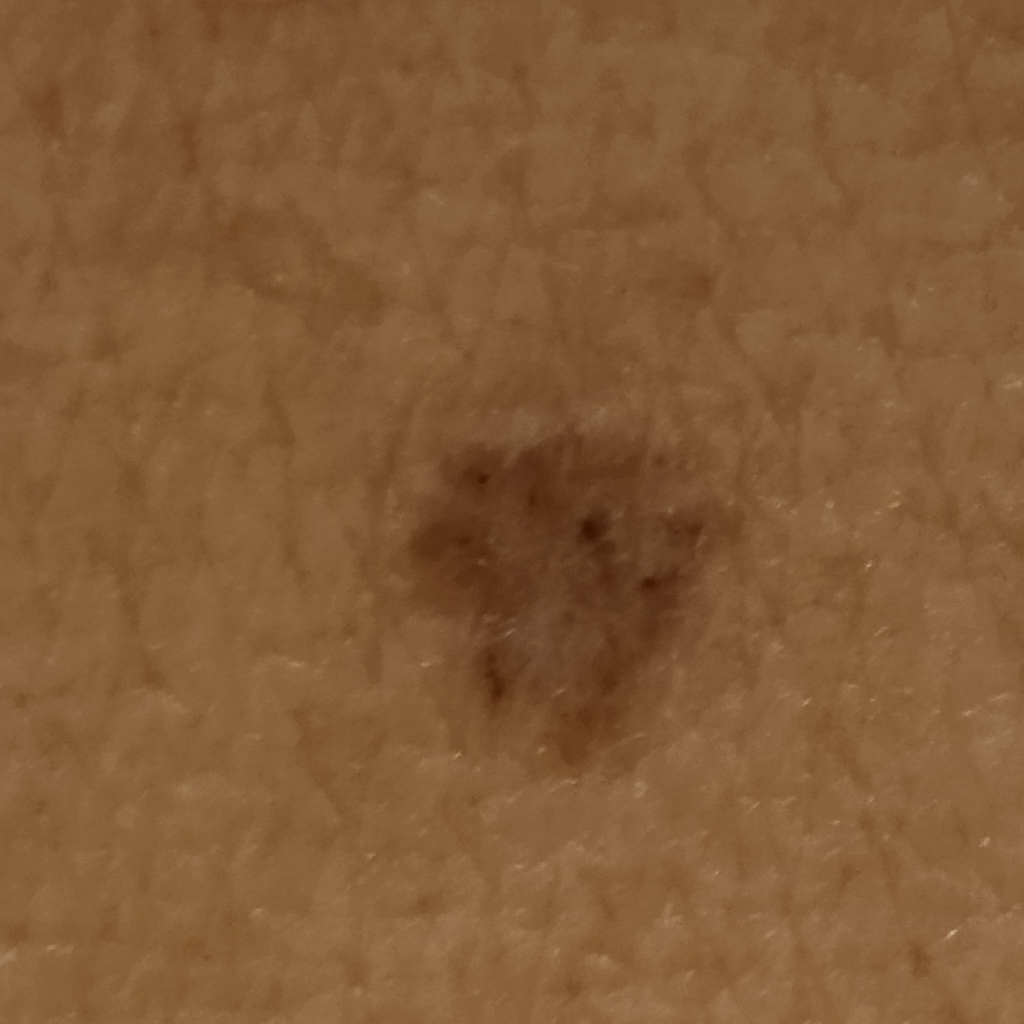{
  "image": "clinical photograph",
  "patient": {
    "age": 60,
    "sex": "female"
  },
  "mole_burden": "few melanocytic nevi overall",
  "referral": "clinical suspicion of basal cell carcinoma",
  "risk_factors": {
    "positive": [
      "a personal history of skin cancer",
      "a personal history of cancer"
    ],
    "negative": [
      "no sunbed use",
      "no family history of skin cancer"
    ]
  },
  "sun_reaction": "skin tans without first burning",
  "lesion_location": "the torso",
  "lesion_size": {
    "diameter_mm": 7.2
  },
  "diagnosis": {
    "name": "basal cell carcinoma",
    "malignancy": "malignant"
  }
}